The patient describes having few moles overall; a female subject 68 years old; on a questionnaire the patient reported no personal history of cancer and no immunosuppression; the patient says their skin tans without first burning; imaged for a research study, with no referral diagnosis recorded; a dermoscopic image of a skin lesion:
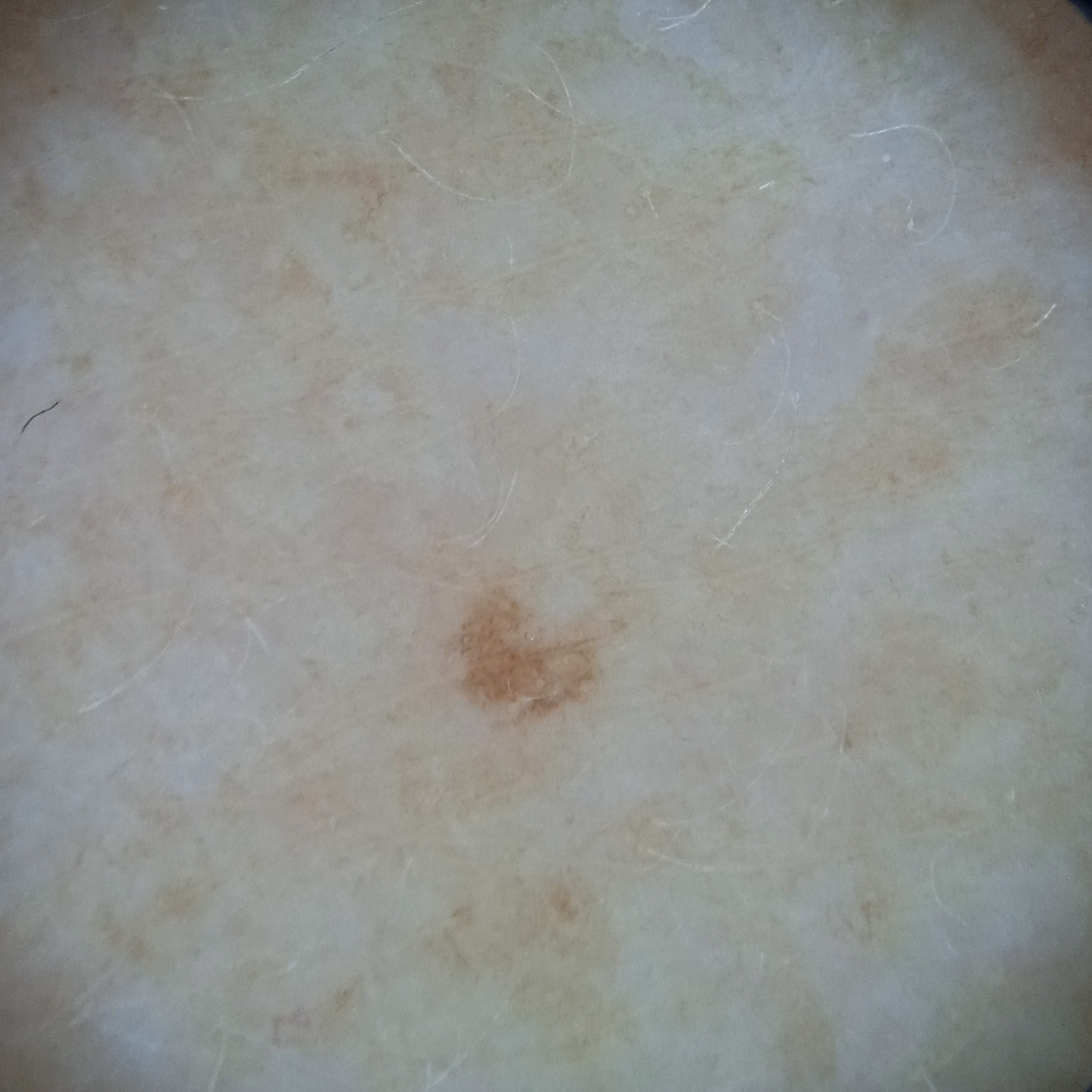Located on an arm. The lesion measures approximately 1.7 mm. The consensus diagnosis for this lesion was a melanocytic nevus.